A dermatoscopic image of a skin lesion:
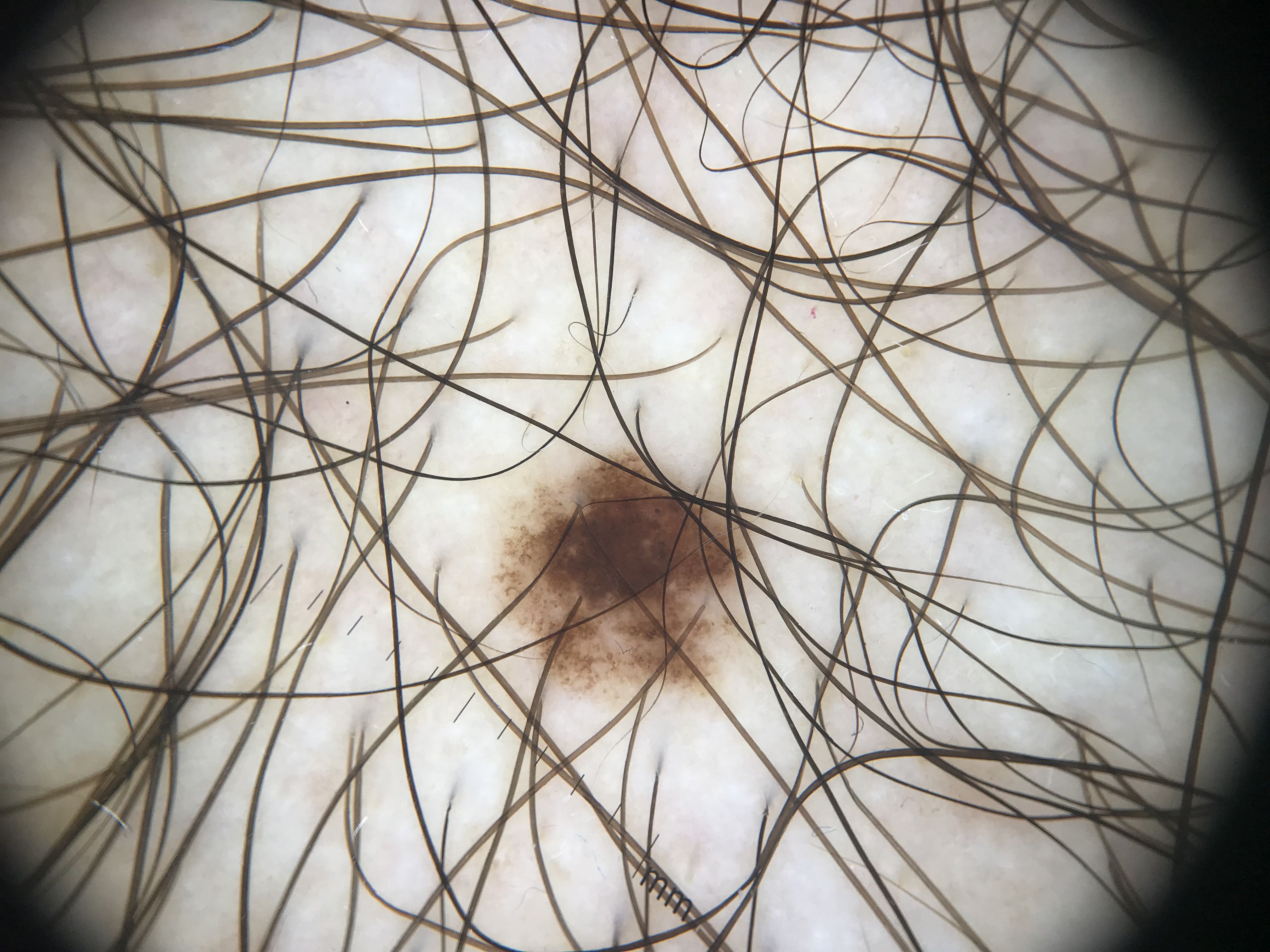diagnostic label: dysplastic junctional nevus (expert consensus).